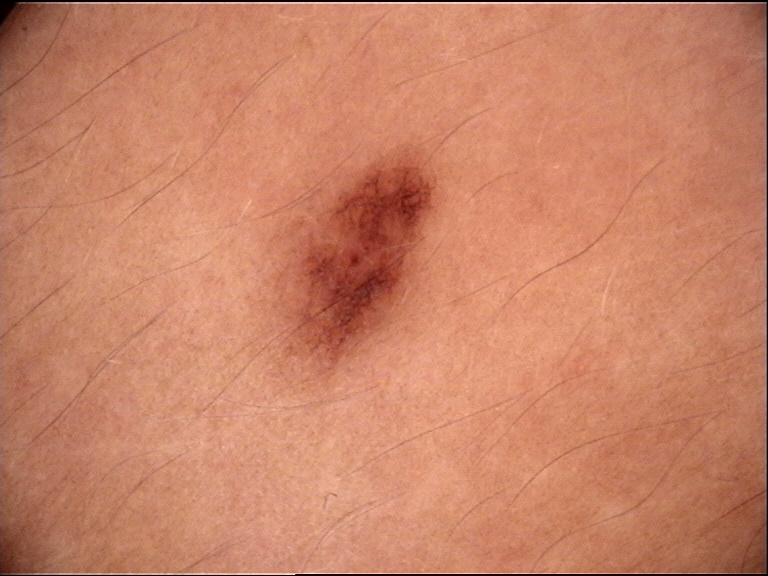A dermoscopic close-up of a skin lesion. Diagnosed as a dysplastic junctional nevus.